A patient age 53 · a smartphone photograph of a skin lesion — 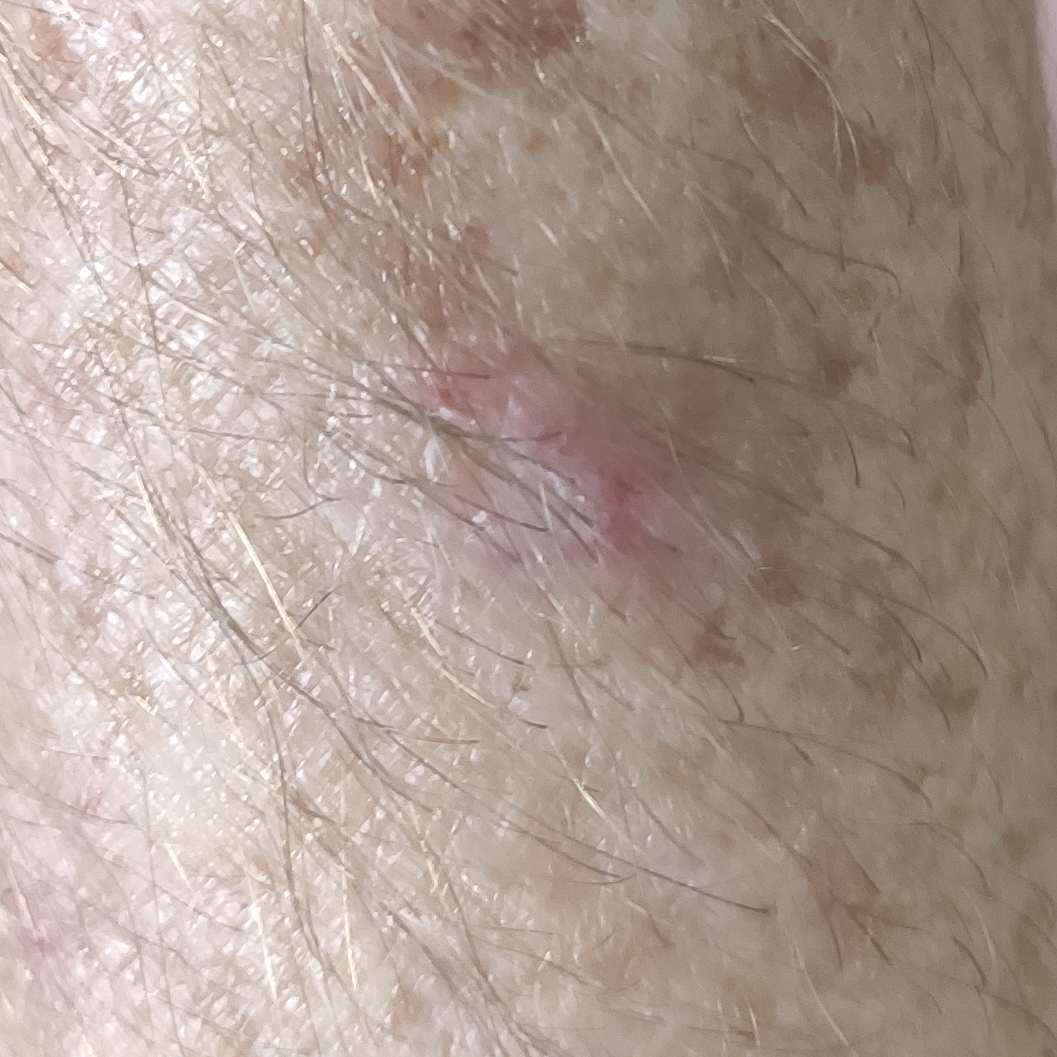{"lesion_location": "a forearm", "symptoms": {"present": ["bleeding", "itching"]}, "diagnosis": {"name": "actinic keratosis", "code": "ACK", "malignancy": "indeterminate", "confirmation": "clinical consensus"}}